An image taken at an angle: 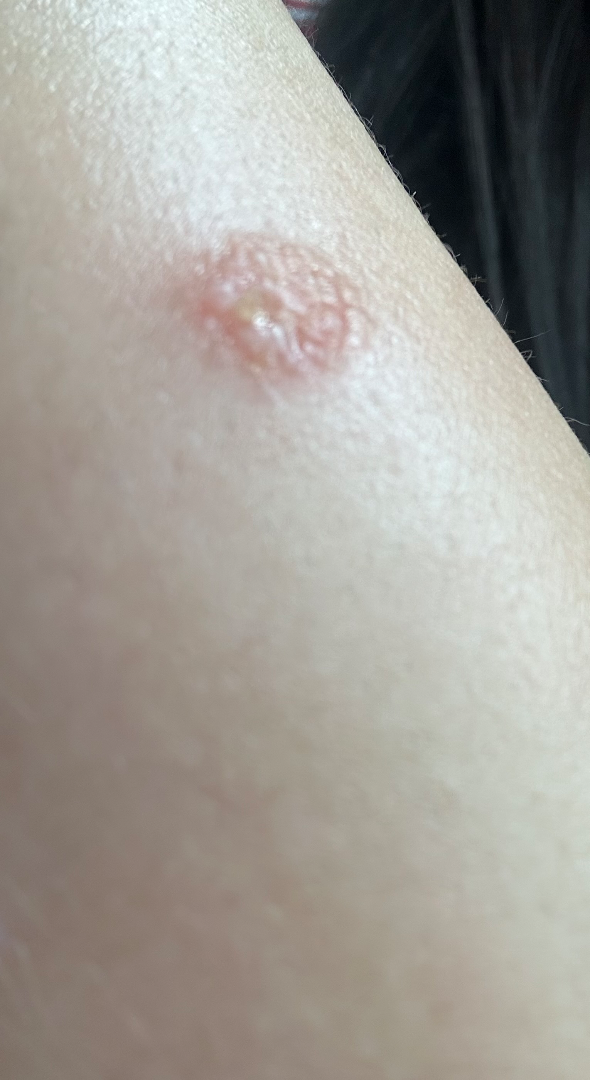assessment: indeterminate.